A dermoscopic image of a skin lesion · the patient was assessed as FST III · a female subject in their 30s: 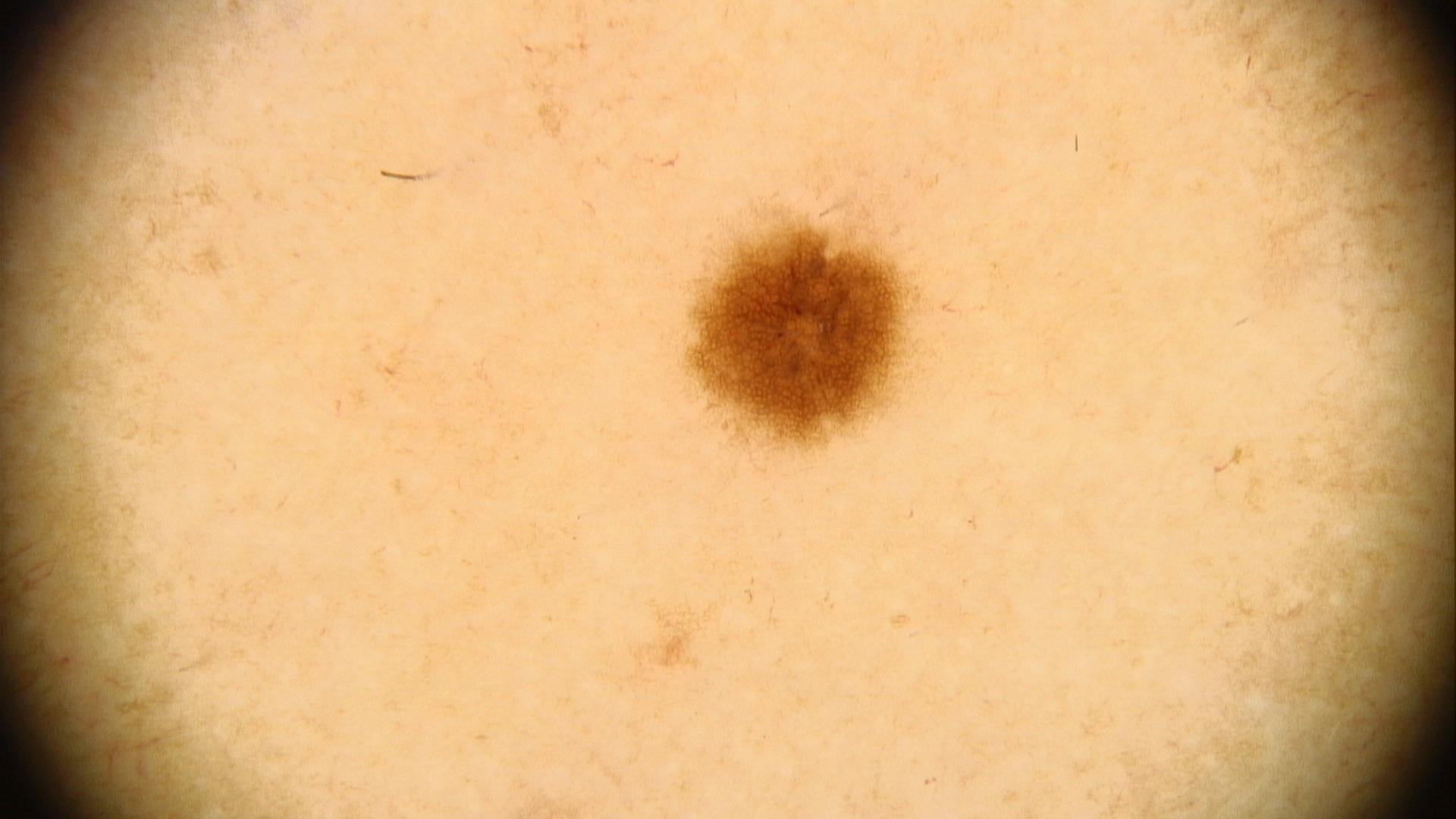The lesion is located on a lower extremity. Expert review favored a nevus.